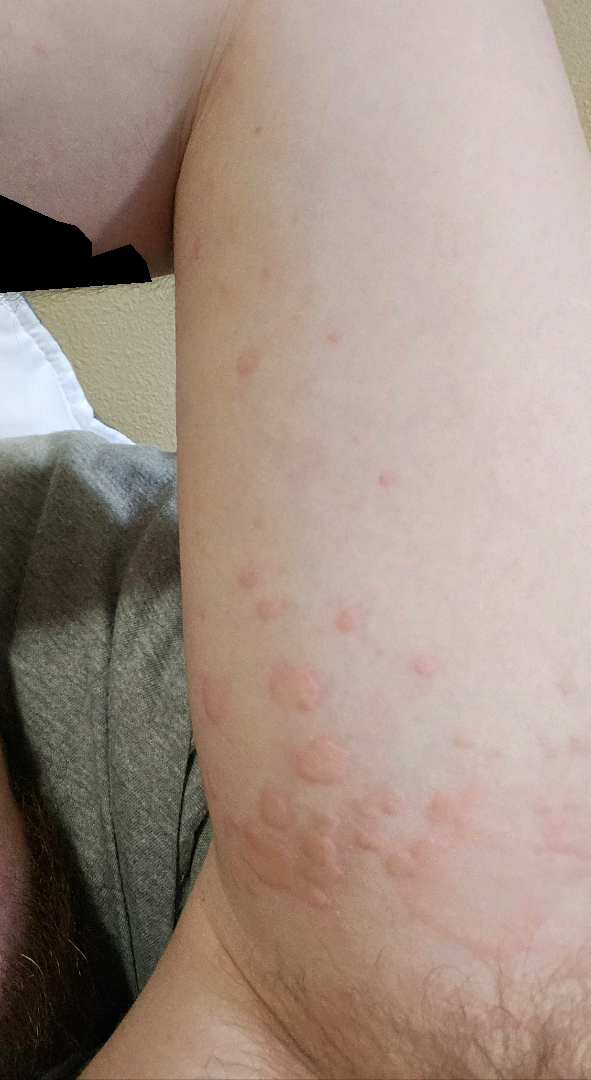The patient considered this a rash. Symptoms reported: enlargement and itching. Close-up view. The patient indicates the lesion is raised or bumpy. The contributor is 30–39, male. The patient indicates the condition has been present for about one day. Located on the front of the torso, leg, arm and back of the torso. On dermatologist assessment of the image, the impression on review was Urticaria.